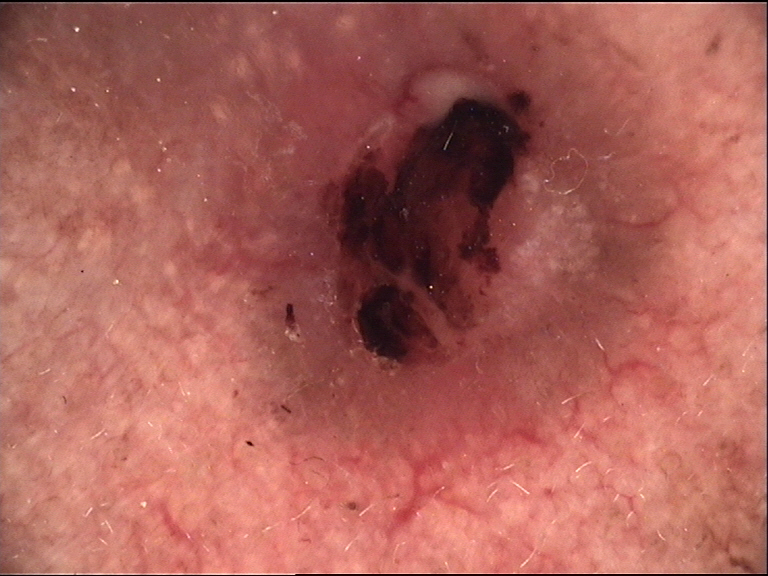modality = dermatoscopy; diagnosis = basal cell carcinoma (biopsy-proven).